Female contributor, age 50–59. The photo was captured at a distance. Located on the top or side of the foot.
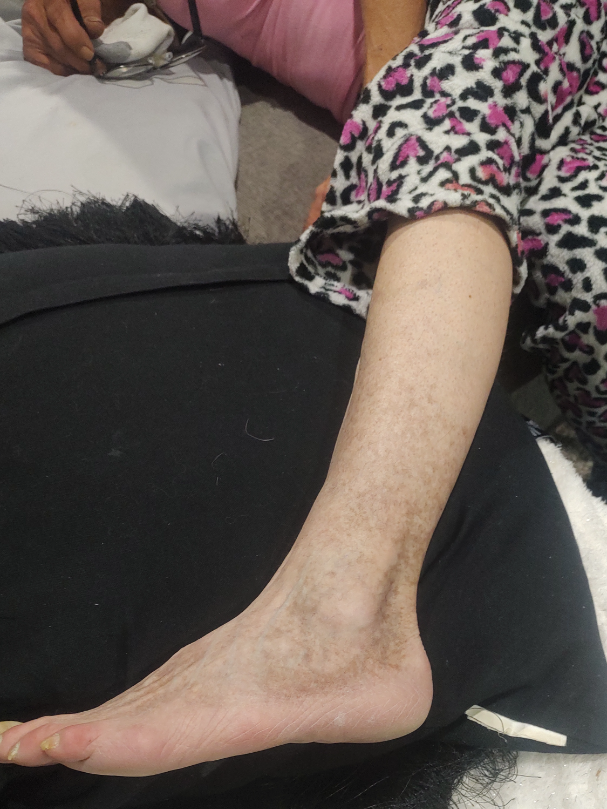One reviewing dermatologist: the impression on review was Hemosiderin pigmentation of skin due to venous insufficiency.